An image taken at an angle. The contributor is 18–29, male. The lesion involves the top or side of the foot — 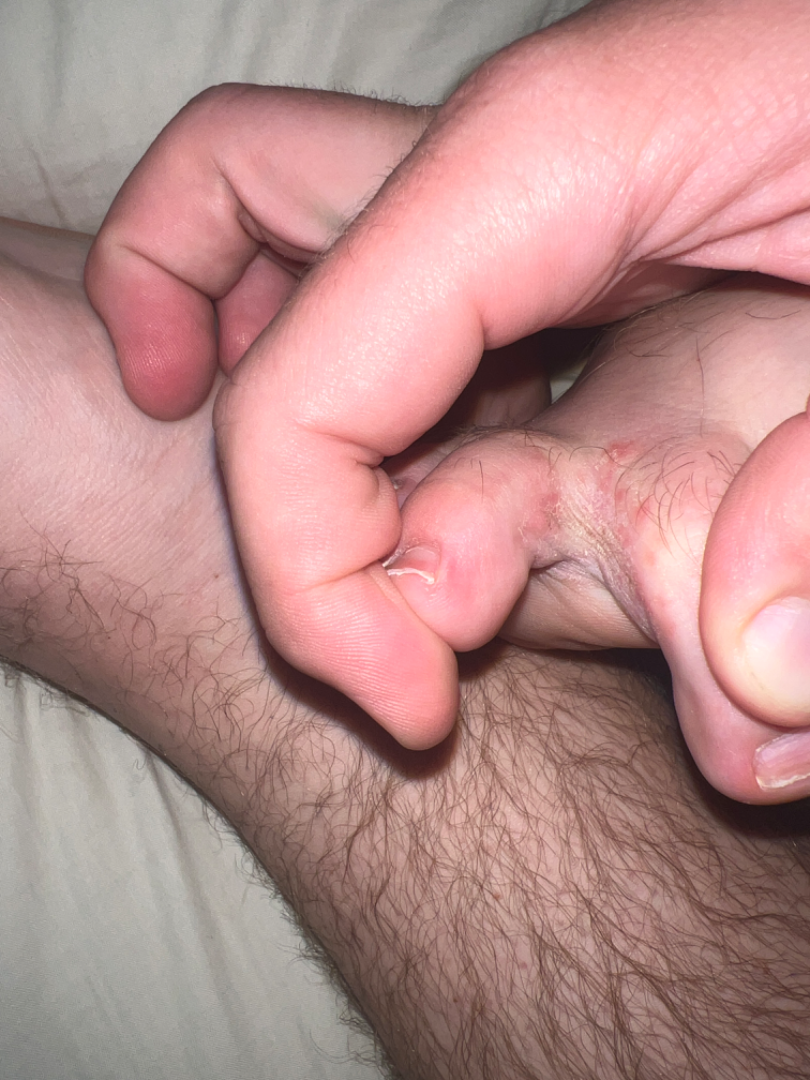Q: What symptoms does the patient report?
A: itching
Q: Patient's own categorization?
A: a rash
Q: When did this start?
A: about one day
Q: Texture?
A: raised or bumpy and rough or flaky
Q: What is the differential diagnosis?
A: most consistent with Tinea; also consider Candida; less probable is Eczema; lower on the differential is Skin and soft tissue atypical mycobacterial infection